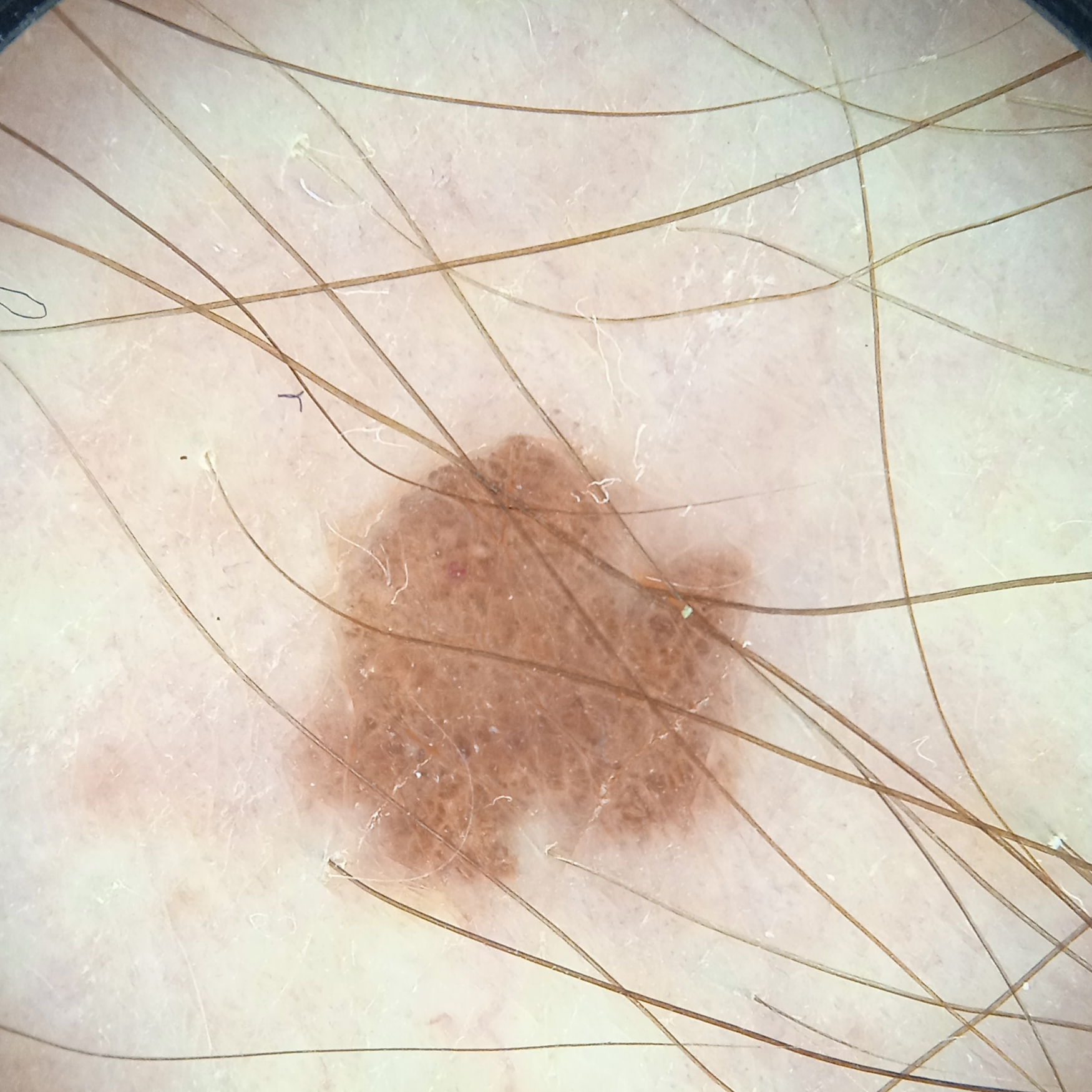Q: Patient demographics?
A: male, aged 65
Q: What is the patient's nevus burden?
A: numerous melanocytic nevi
Q: What is the referral context?
A: research study (no referral diagnosis)
Q: What are the relevant risk factors?
A: immunosuppression, a family history of skin cancer, a personal history of skin cancer
Q: What is the imaging modality?
A: dermatoscopic image
Q: How large is the lesion?
A: 5.5 mm
Q: What was the diagnosis?
A: melanocytic nevus (dermatologist consensus)